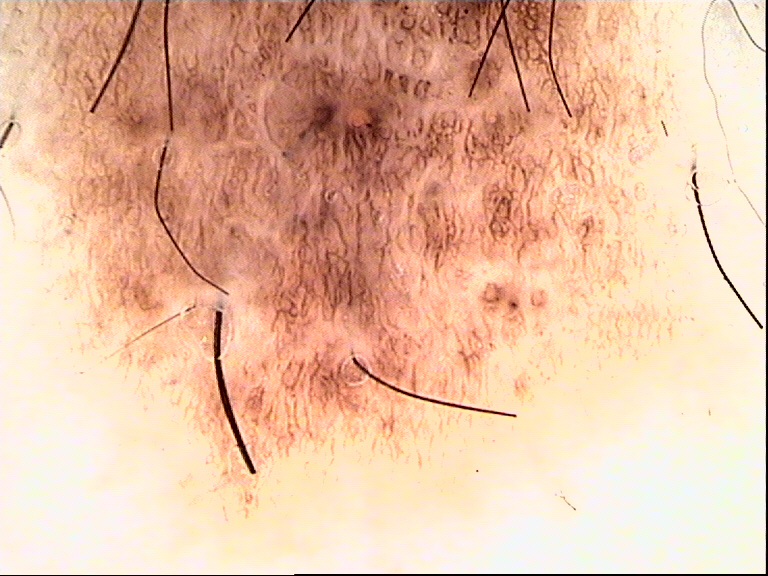The diagnosis was a congenital compound nevus.